Located on the head or neck; this is a close-up image.
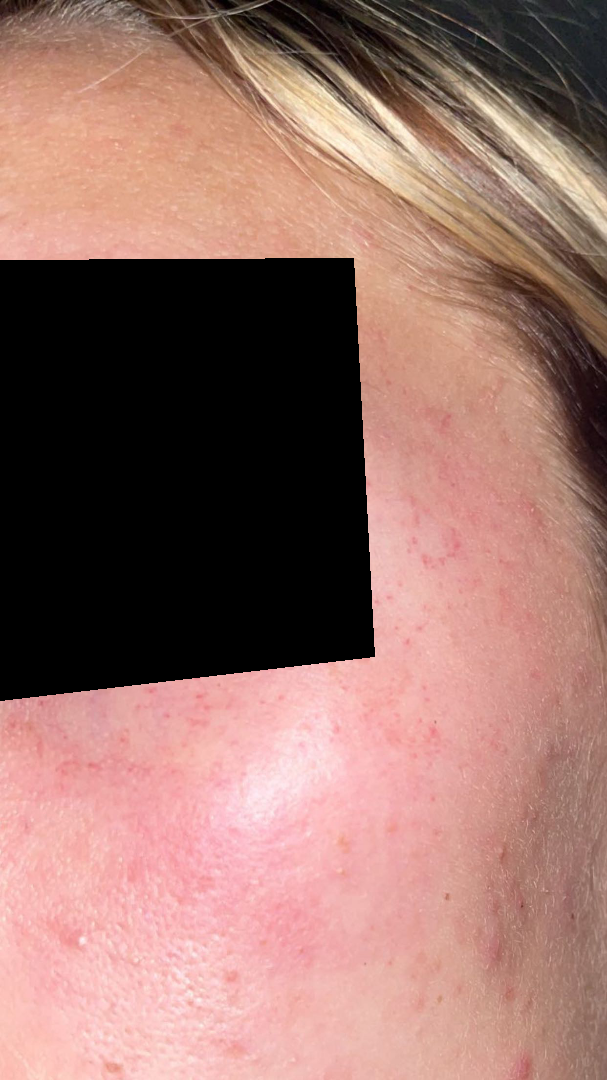Most likely Rosacea; also consider Acne.